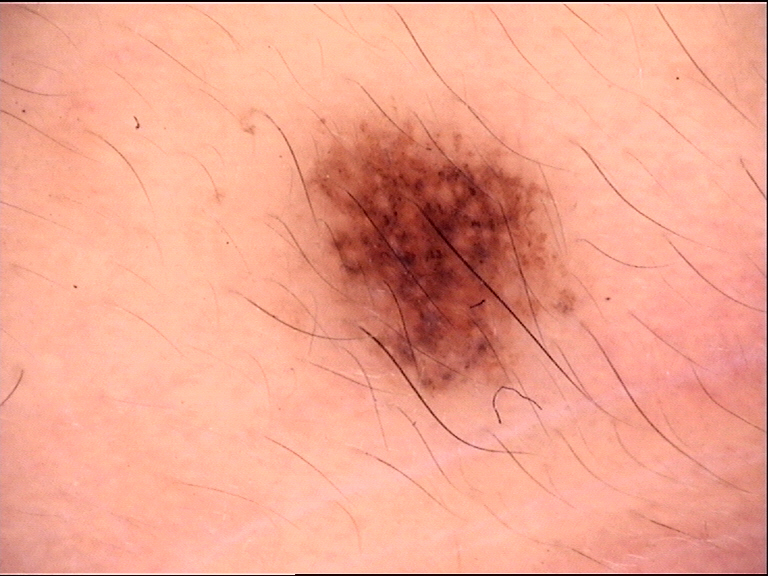modality = dermoscopy
label = Miescher nevus (expert consensus)